The contributor reports associated joint pain; the arm is involved; texture is reported as flat; the contributor reports the condition has been present for about one day; a close-up photograph: 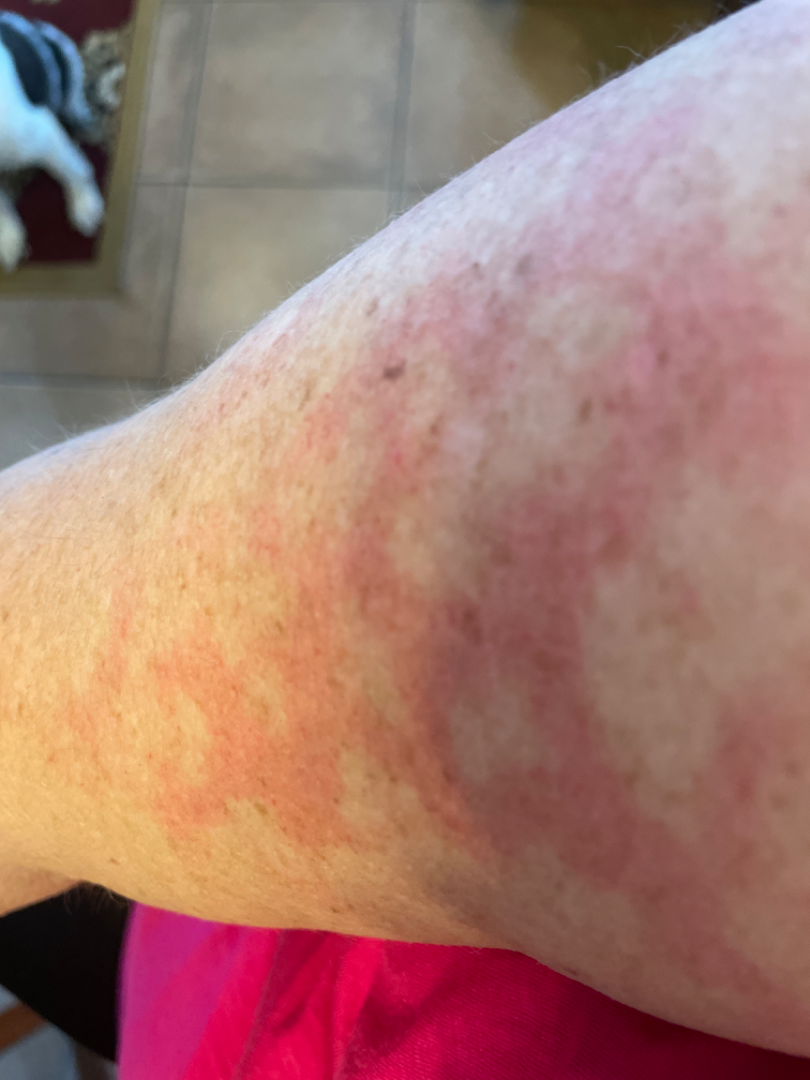Assessment:
Livedo reticularis, Erythema ab igne and Livedoid vasculopathy were each considered, in no particular order.